The photograph was taken at a distance, the patient reports the lesion is raised or bumpy — 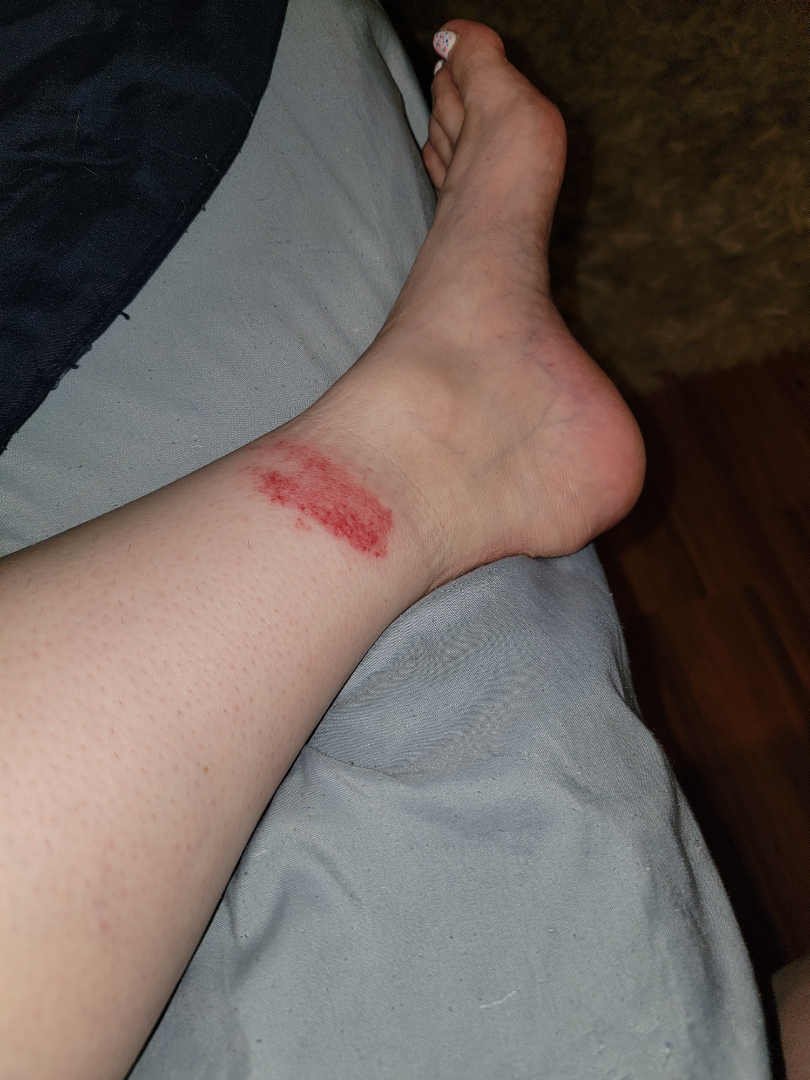Impression: On dermatologist assessment of the image: Eczema, Allergic Contact Dermatitis and Irritant Contact Dermatitis were each considered, in no particular order.